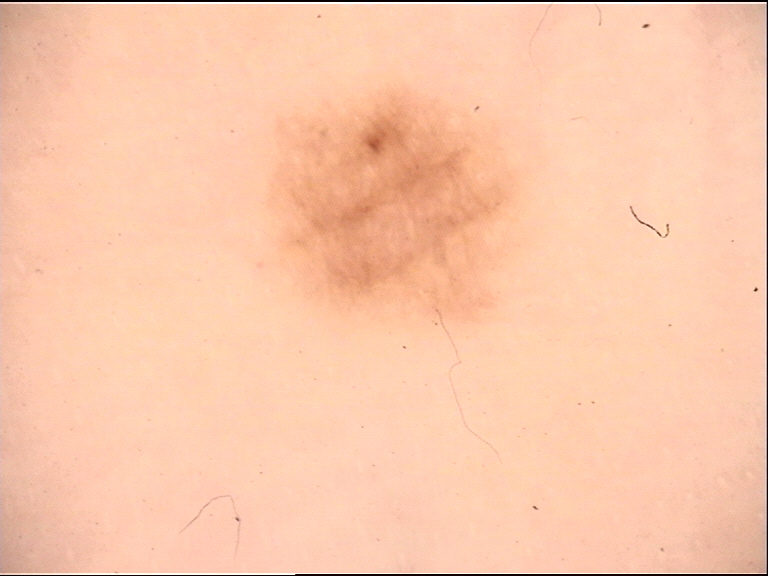Case:
• image — dermatoscopy
• diagnosis — acral junctional nevus (expert consensus)